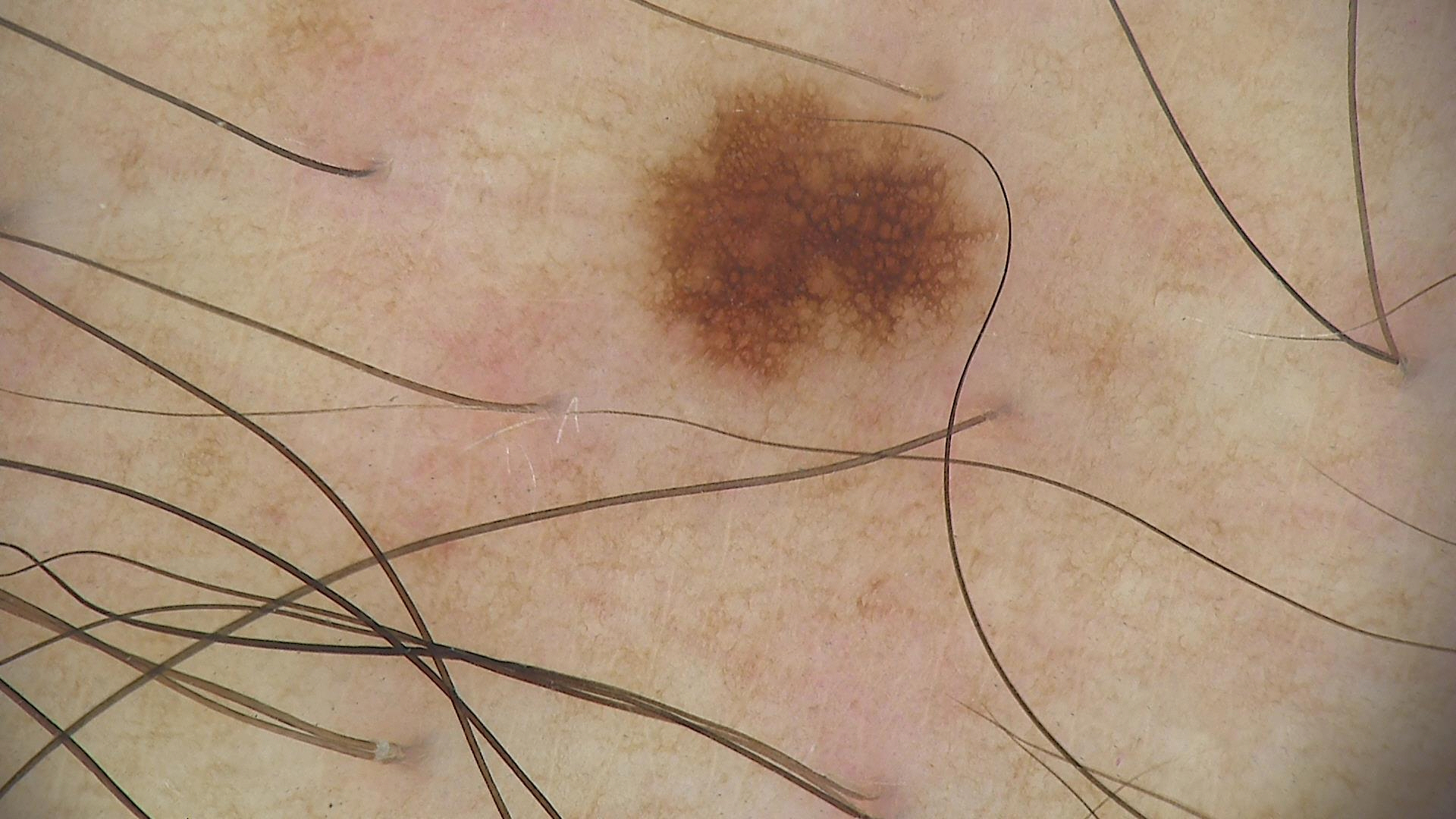Findings:
– label · dysplastic junctional nevus (expert consensus)